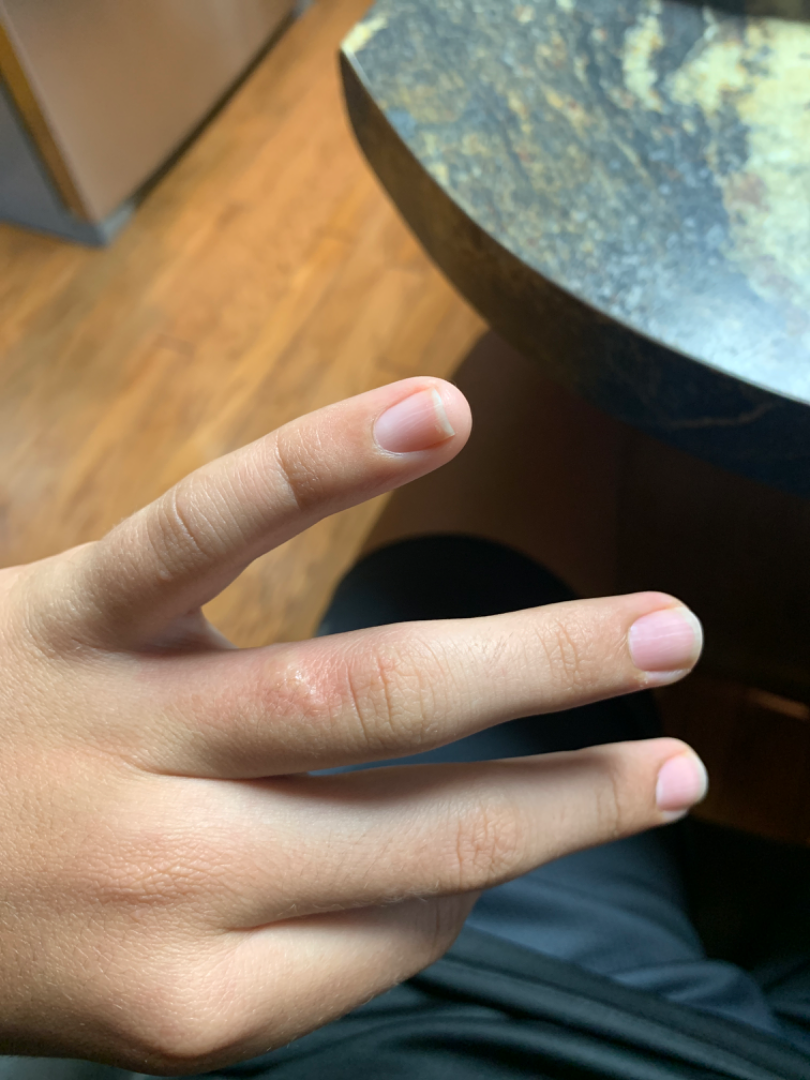assessment = unable to determine
present for = about one day
view = at an angle
texture = fluid-filled
other reported symptoms = mouth sores
patient-reported symptoms = itching, pain and enlargement
subject = male, age 18–29
skin tone = self-reported Fitzpatrick skin type IV; non-clinician graders estimated 1 on the Monk Skin Tone